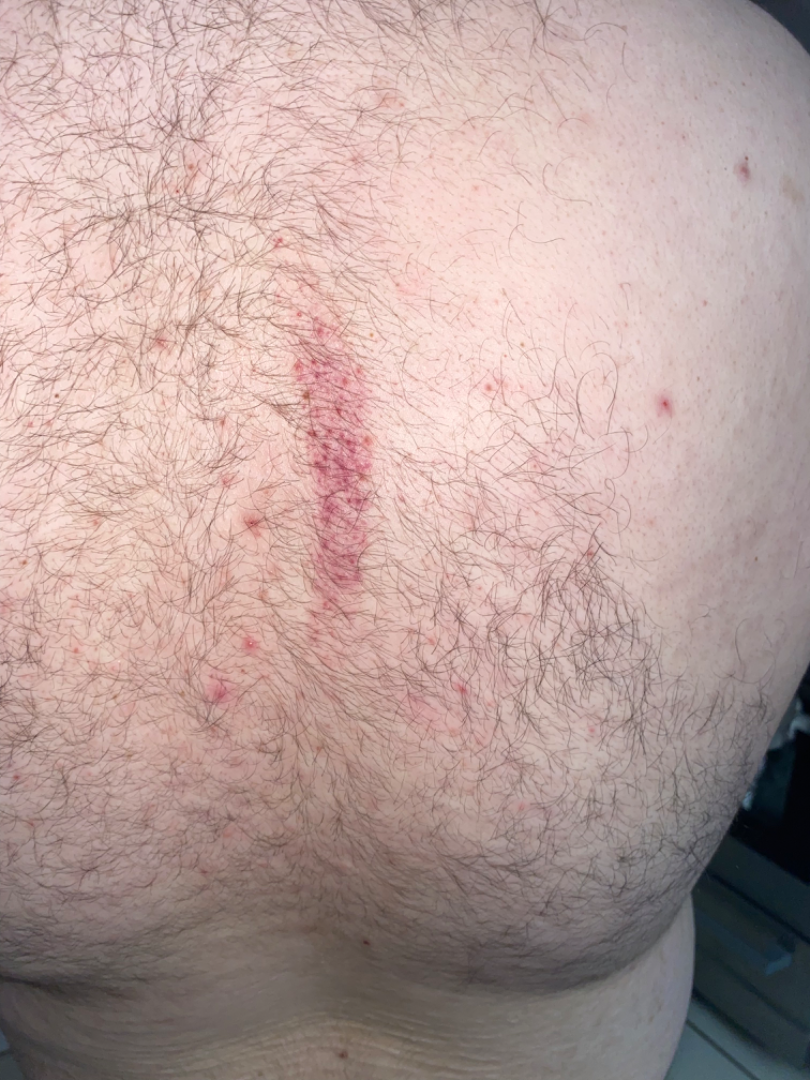This is a close-up image.
On teledermatology review: Abrasion, scrape, or scab; Benign cutaneous vascular tumor; and ecchymoses were considered with similar weight.